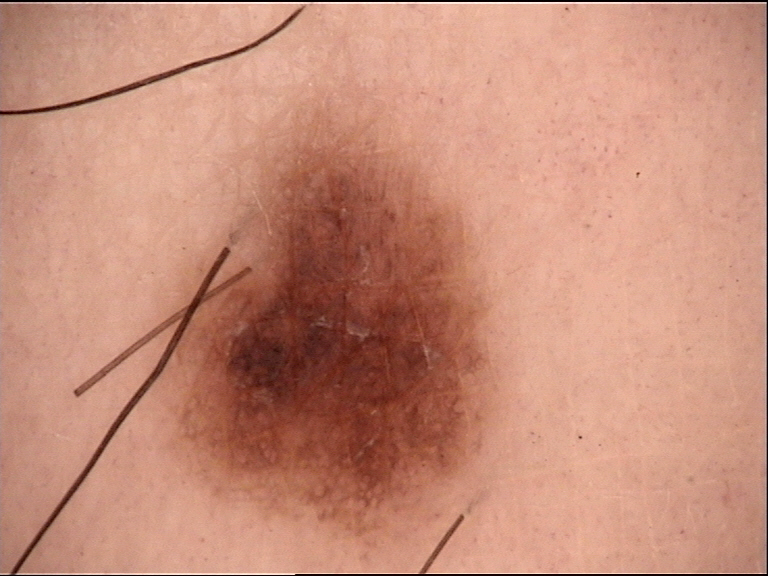Diagnosed as a banal lesion — a junctional nevus.